A dermoscopic view of a skin lesion, the subject is a male aged 58 to 62:
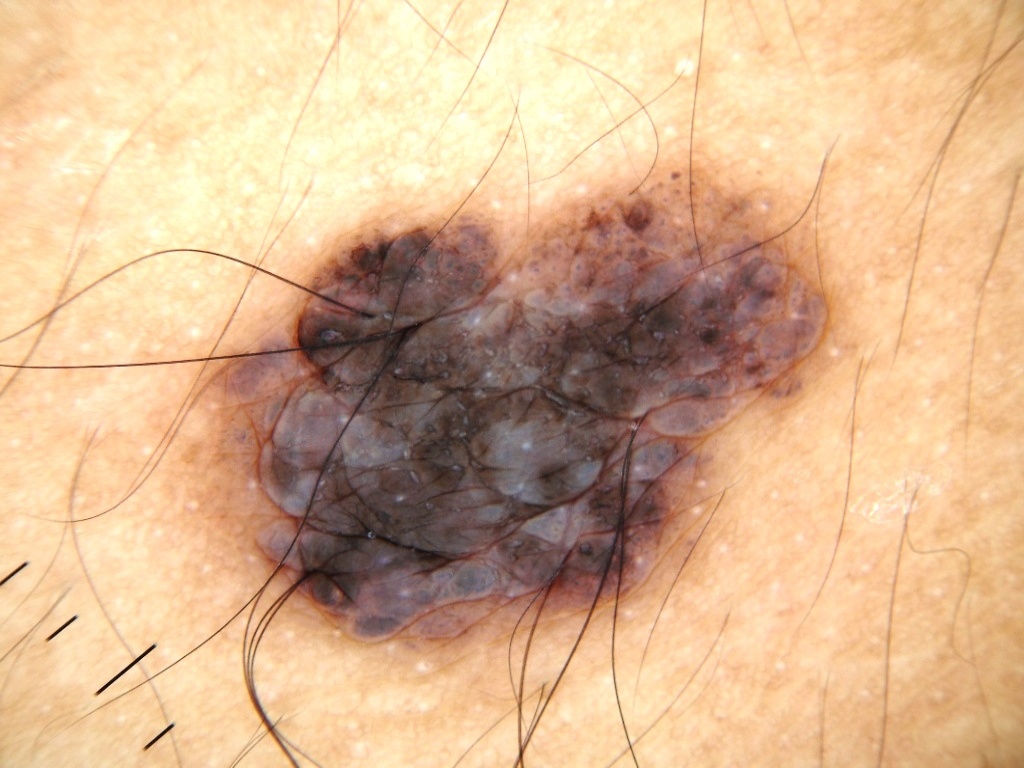bounding box=(165, 150, 843, 666) | dermoscopic findings=milia-like cysts | diagnostic label=a melanocytic nevus.